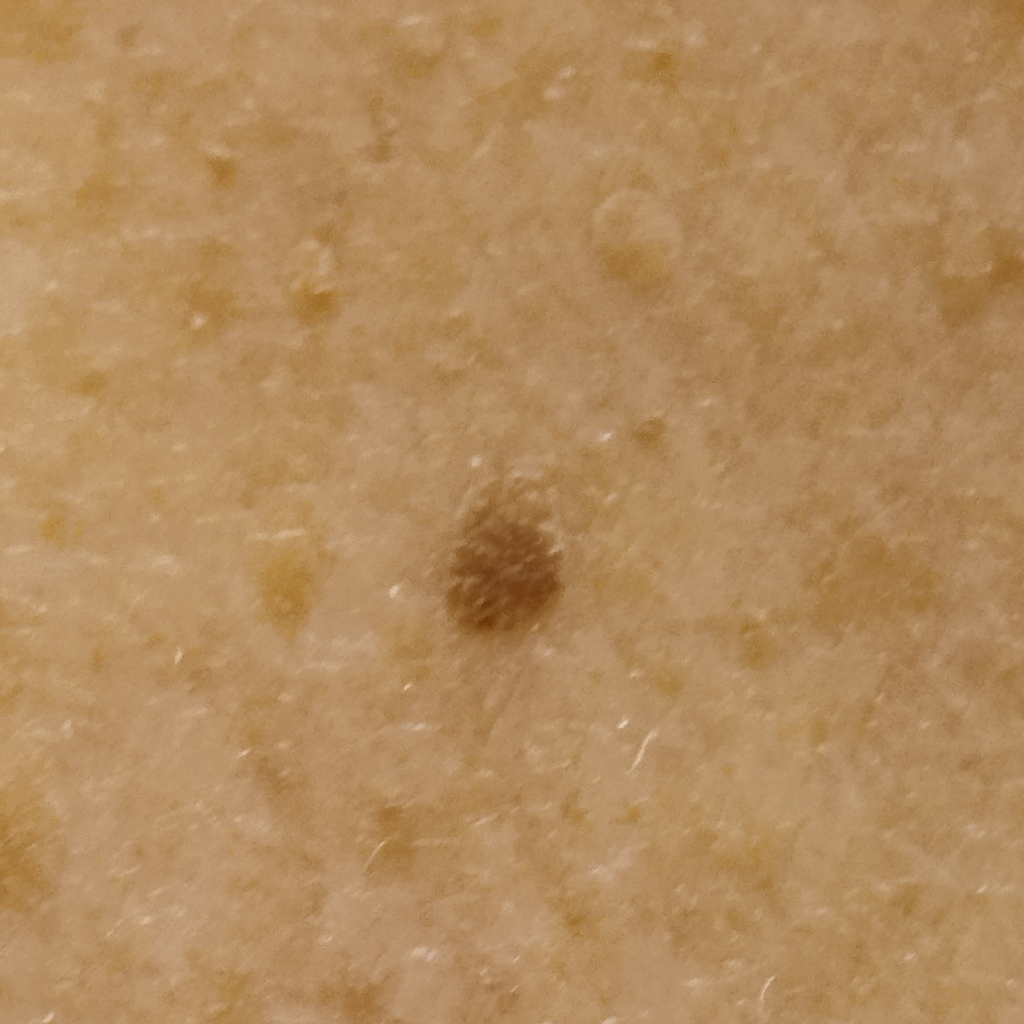Q: Patient demographics?
A: male, 62 years old
Q: What is the patient's nevus burden?
A: few melanocytic nevi overall
Q: How does the patient's skin react to sun?
A: skin reddens with sun exposure
Q: What kind of image is this?
A: clinical photograph
Q: What is the anatomic site?
A: the back
Q: What was the diagnosis?
A: seborrheic keratosis (dermatologist consensus)